A dermoscopy image of a single skin lesion: 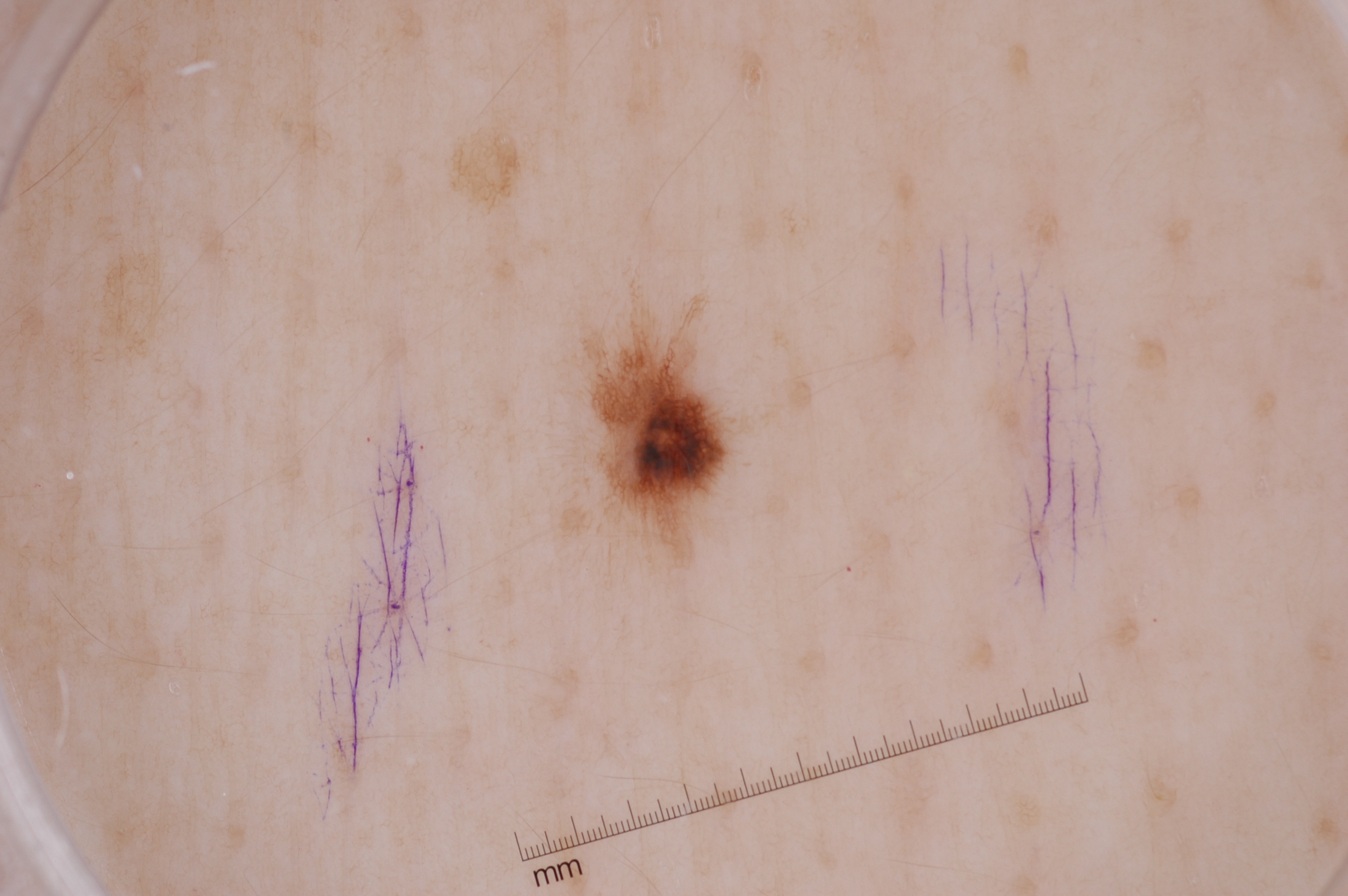Q: What is the lesion's bounding box?
A: 550/256/757/592
Q: What is this lesion?
A: a melanocytic nevus, a benign lesion